The affected area is the leg; the contributor reports the lesion is raised or bumpy; this is a close-up image; the patient described the issue as a rash; reported duration is about one day; the contributor reports bothersome appearance and itching — 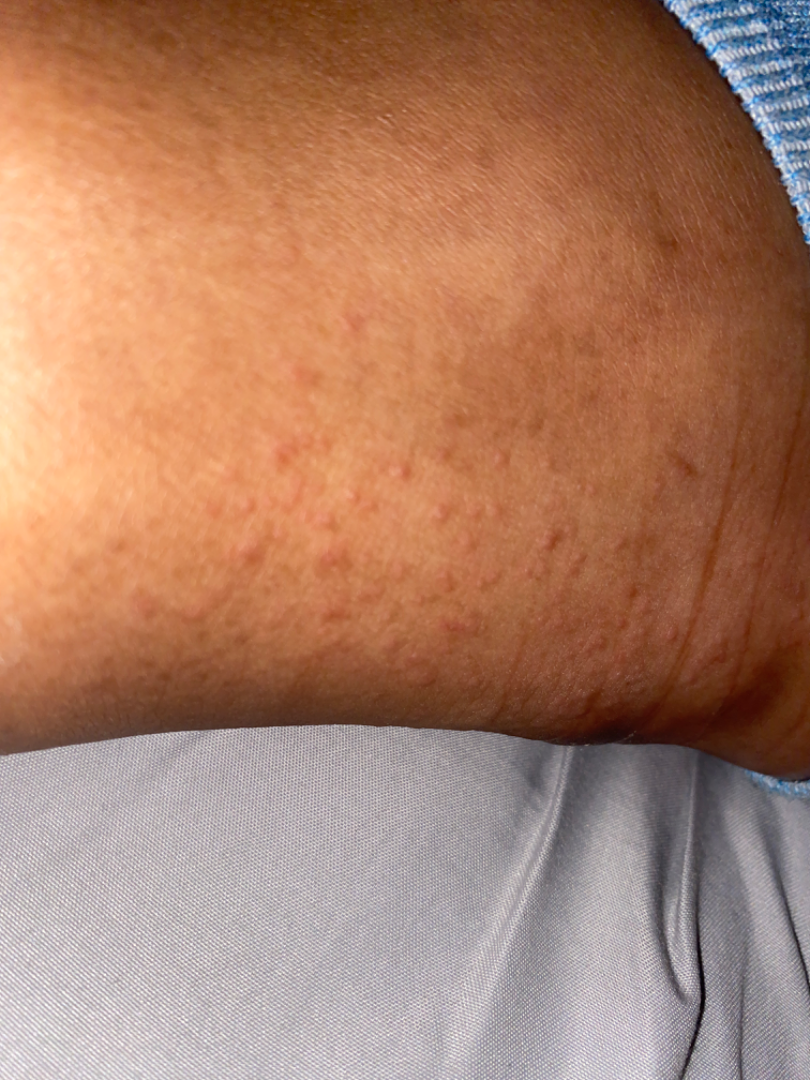Most consistent with Eczema; possibly Lichen planus/lichenoid eruption.